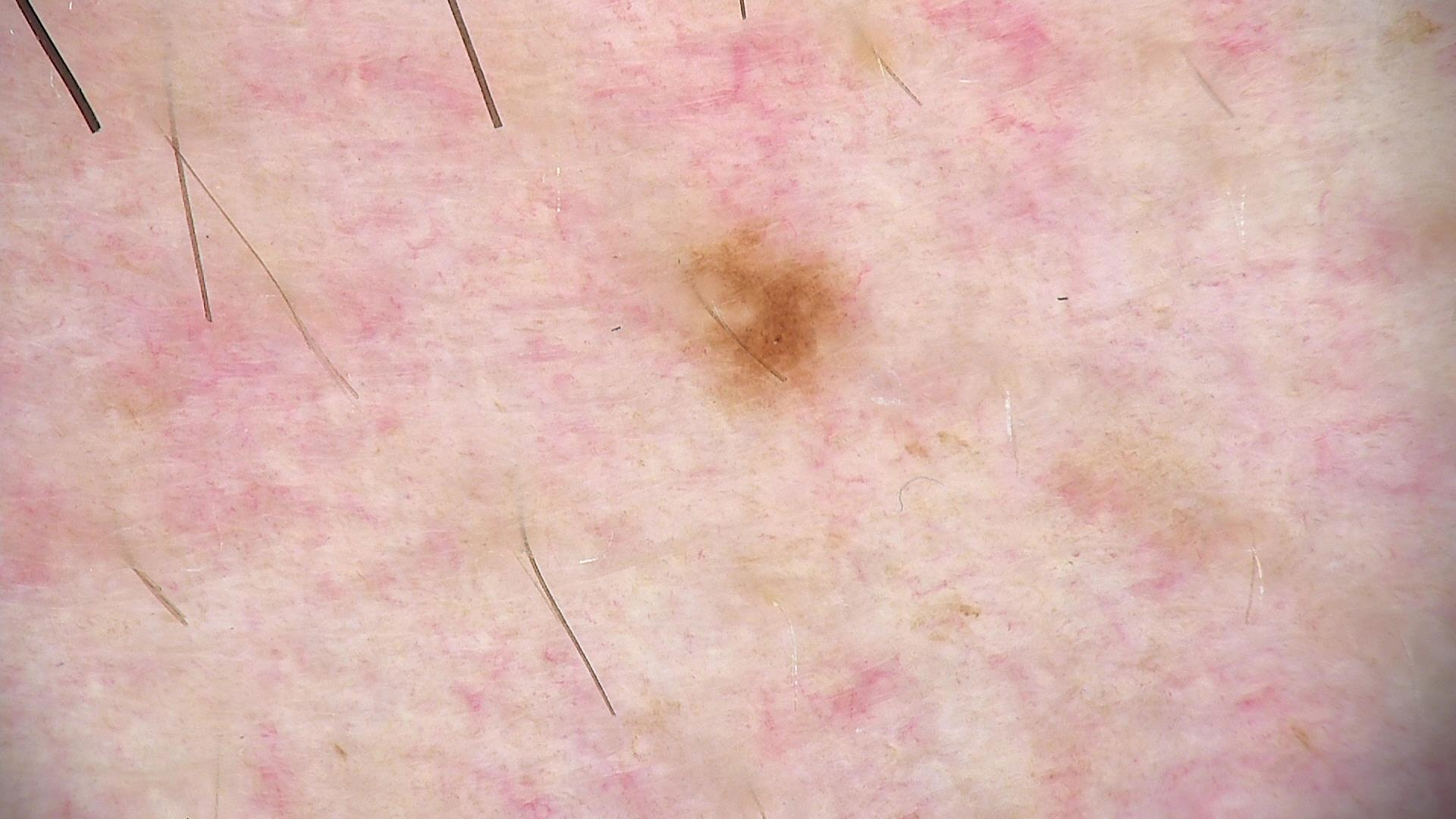A skin lesion imaged with a dermatoscope.
Classified as a dysplastic junctional nevus.